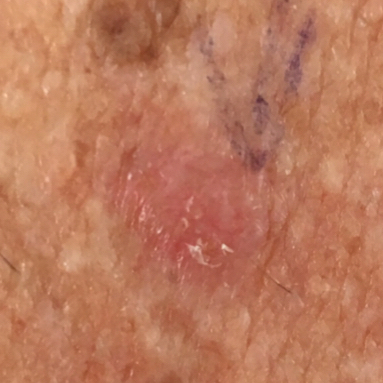The patient is Fitzpatrick phototype II. By history, pesticide exposure, prior skin cancer (patient or family), prior malignancy (patient or family), and alcohol use. A male subject in their early 50s. A smartphone photograph of a skin lesion. The lesion is on the chest. Measuring about 9 × 5 mm. The patient reports that the lesion itches, hurts, has grown, has bled, and is elevated, but has not changed. Histopathology confirmed a basal cell carcinoma.